A dermoscopy image of a single skin lesion. The patient is a female aged 53-57.
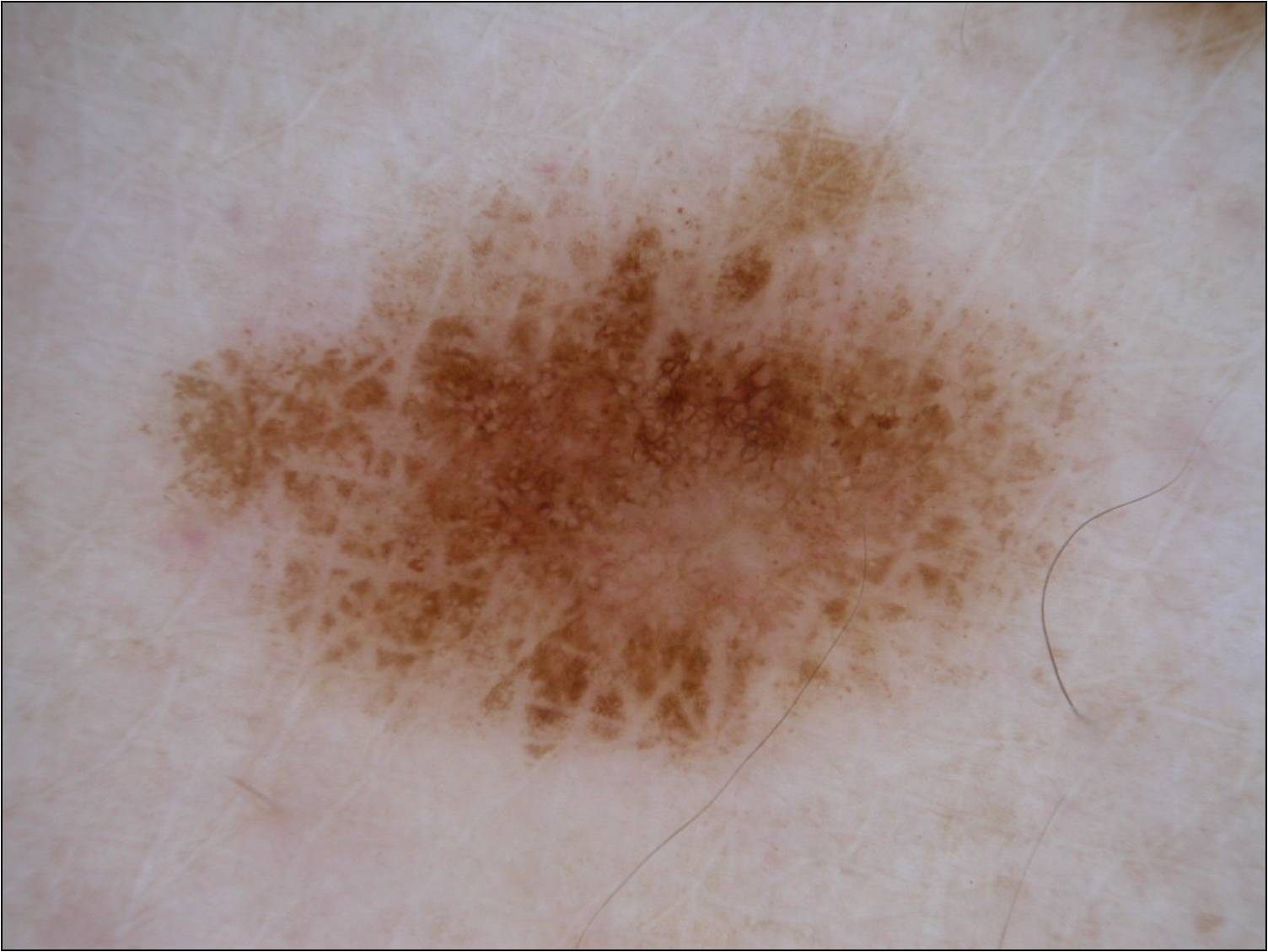dermoscopic_features:
  present:
    - pigment network
    - globules
  absent:
    - negative network
    - streaks
    - milia-like cysts
lesion_extent: large
lesion_location:
  bbox_xyxy:
    - 132
    - 77
    - 1158
    - 783
diagnosis:
  name: melanoma
  malignancy: malignant
  lineage: melanocytic
  provenance: histopathology